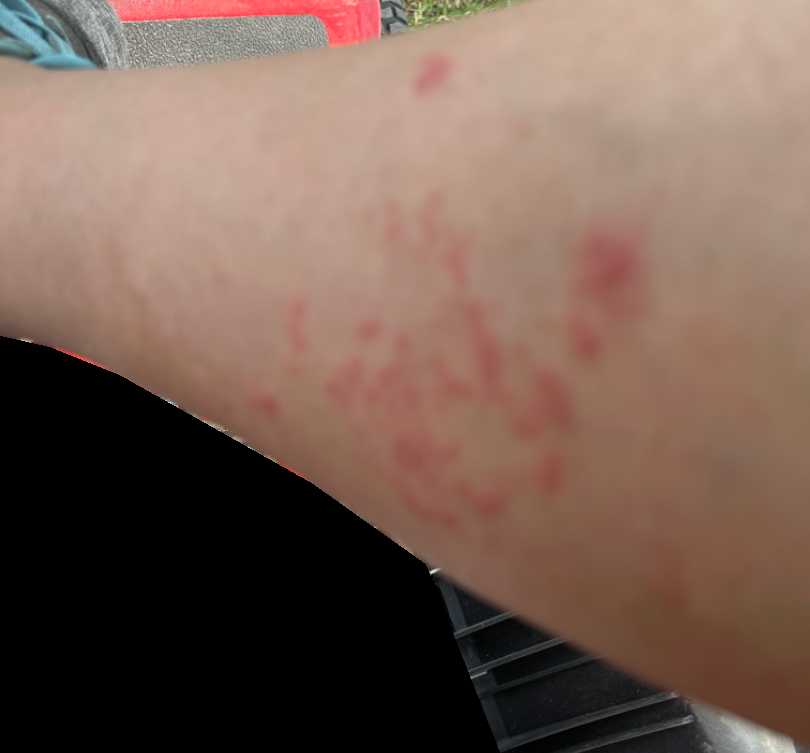Findings:
- assessment — not assessable